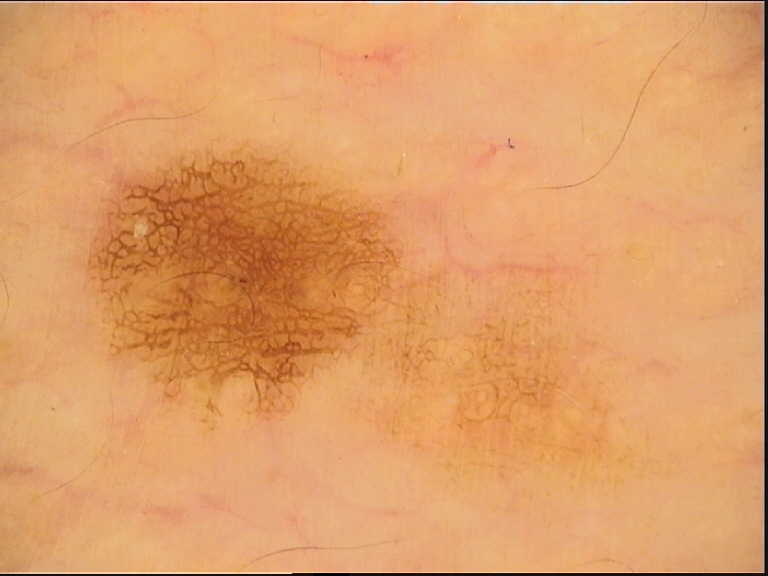  diagnosis:
    name: dysplastic junctional nevus
    code: jd
    malignancy: benign
    super_class: melanocytic
    confirmation: expert consensus